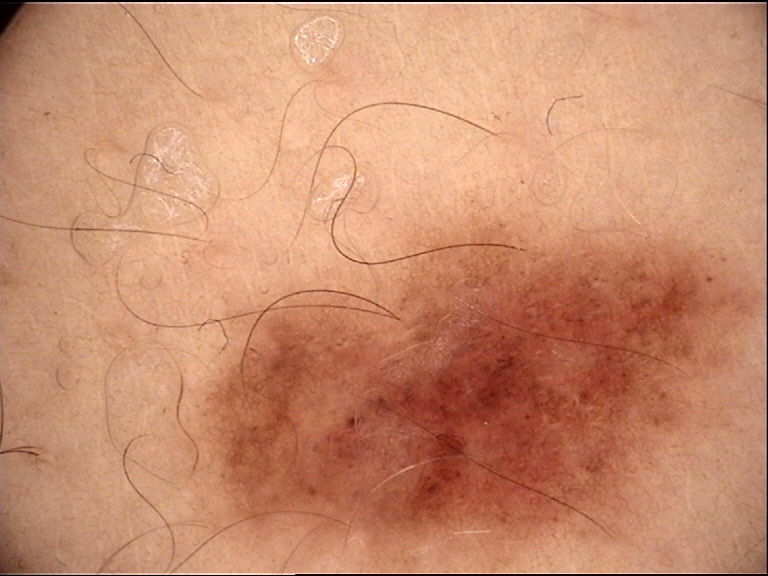A dermoscopic photograph of a skin lesion. Classified as a benign lesion — a dysplastic junctional nevus.